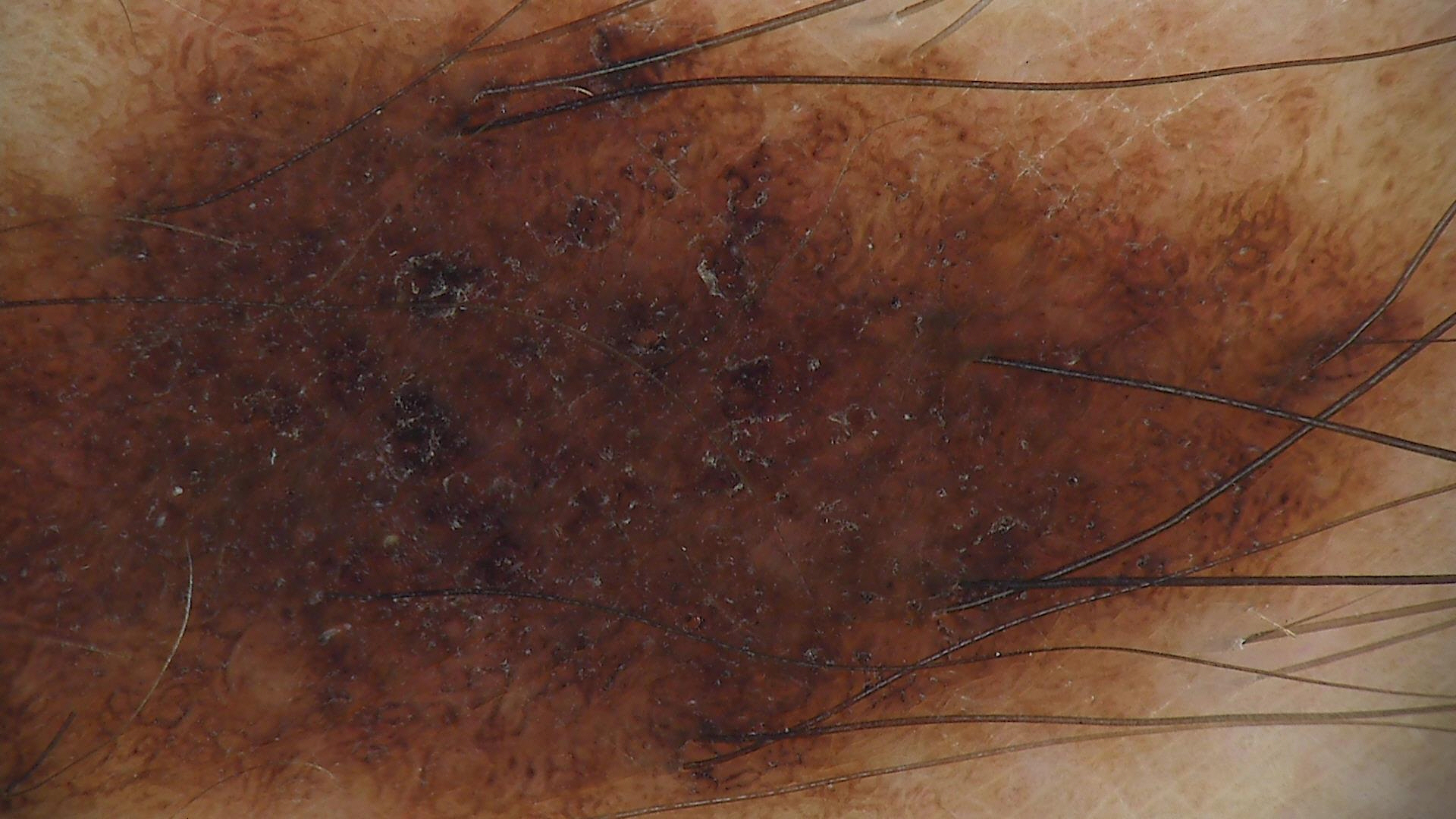{"diagnosis": {"name": "congenital dysplastic compound nevus", "code": "ccd", "malignancy": "benign", "super_class": "melanocytic", "confirmation": "expert consensus"}}